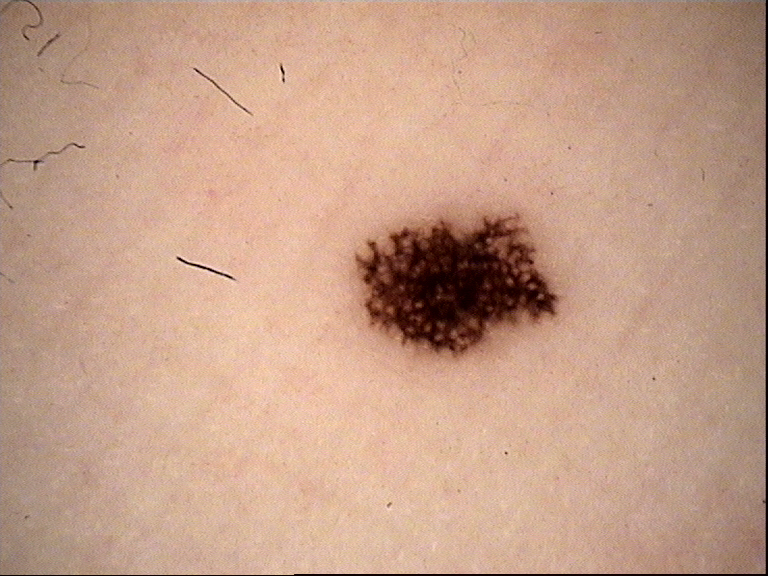imaging: dermoscopy; diagnostic label: acral dysplastic junctional nevus (expert consensus).